Dermoscopy of a skin lesion.
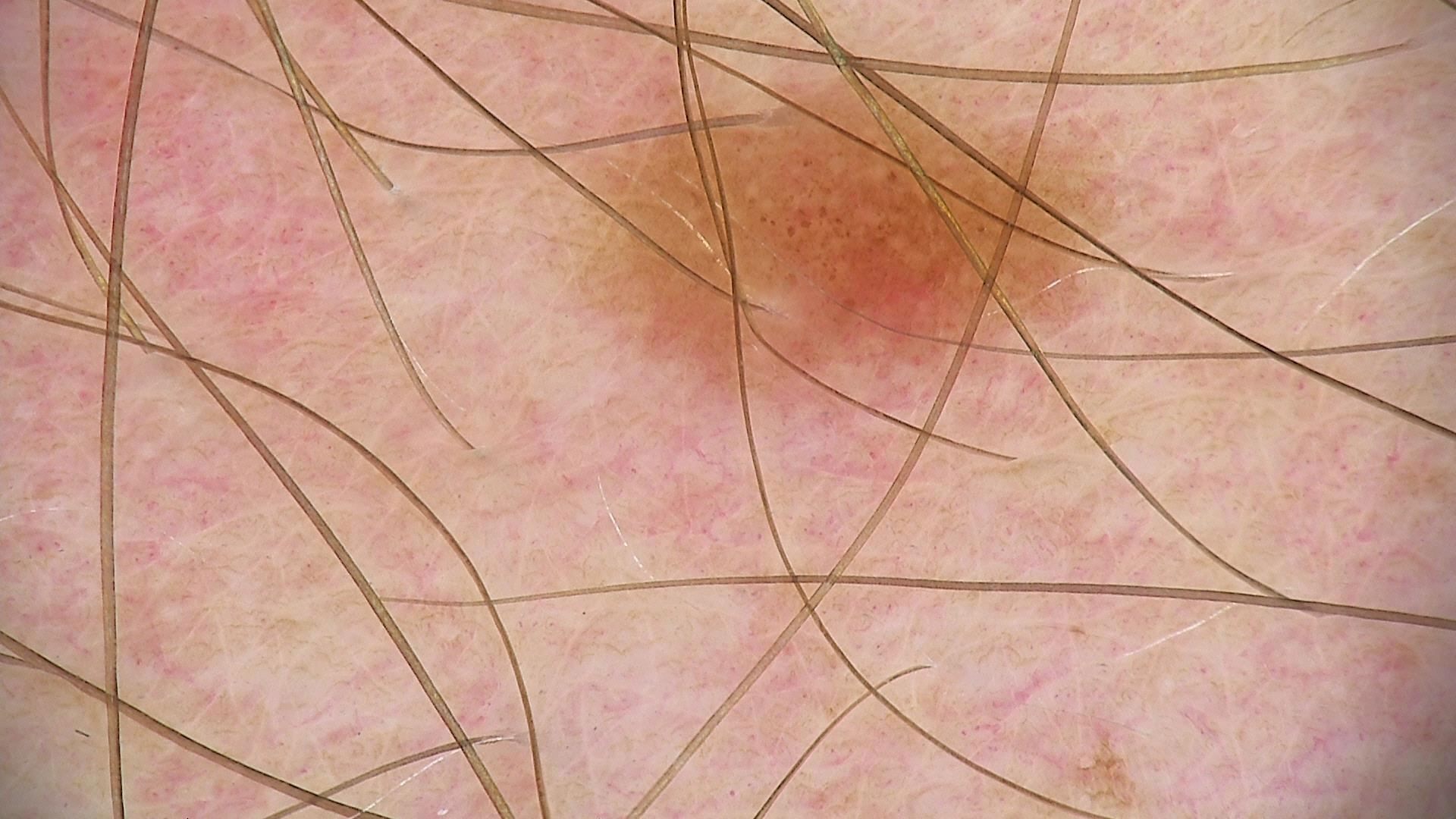The diagnostic label was a banal lesion — a junctional nevus.